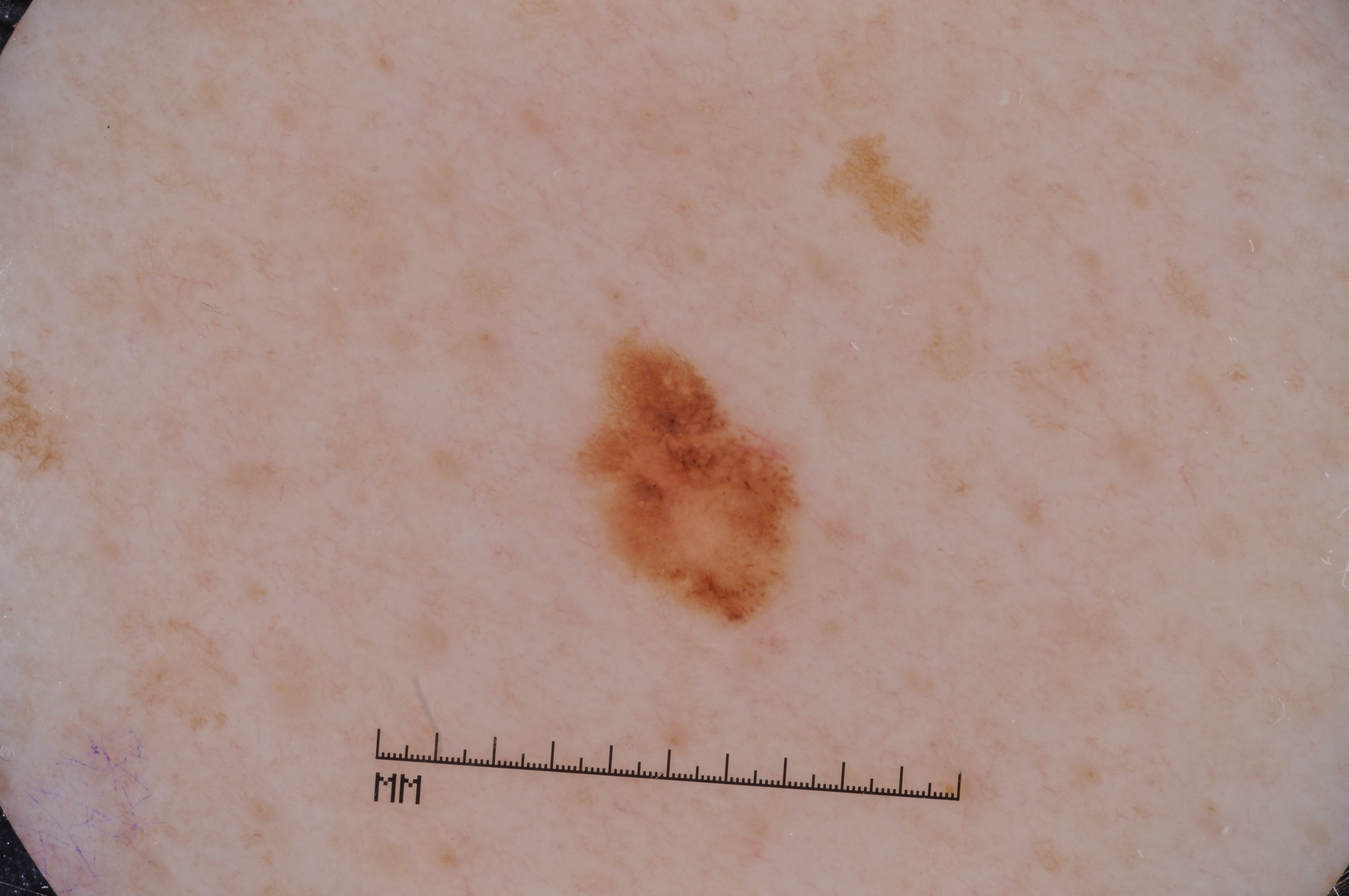A dermatoscopic image of a skin lesion. The subject is a male aged 63 to 67. Dermoscopically, the lesion shows pigment network and milia-like cysts. The lesion is bounded by x1=567, y1=326, x2=806, y2=635. The lesion covers approximately 4% of the dermoscopic field. Histopathological examination showed a melanoma.